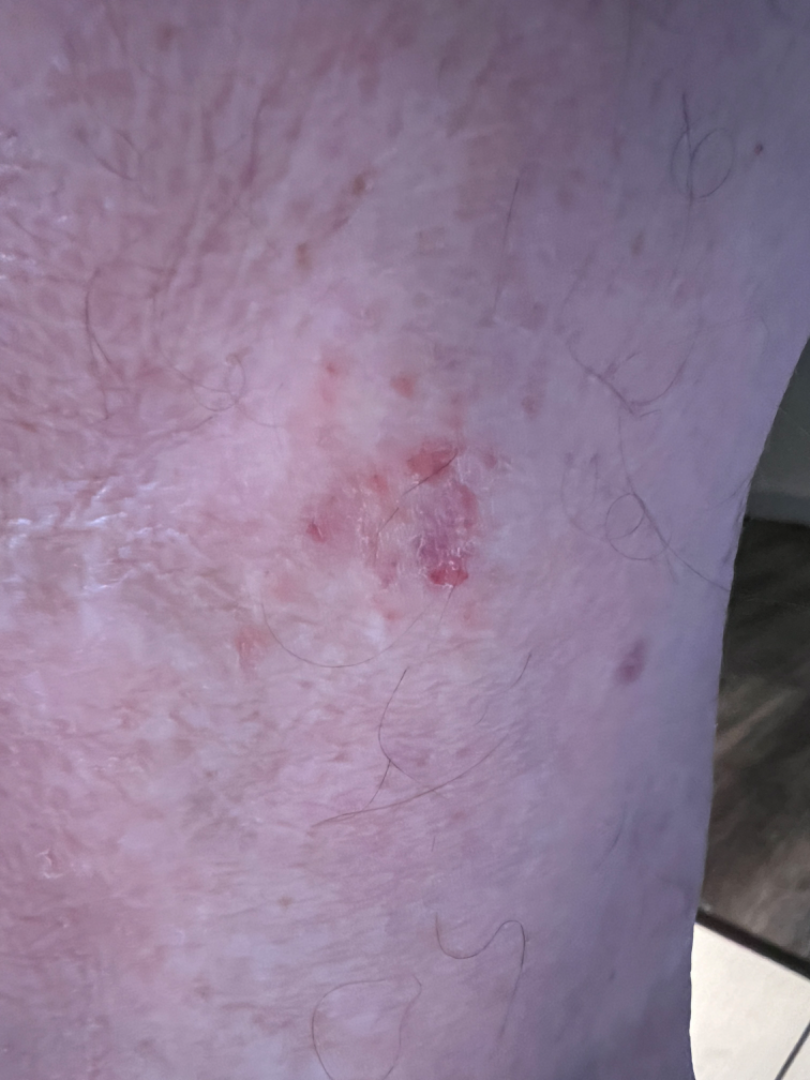{"shot_type": "close-up", "body_site": "leg", "patient": "male, age 60–69", "differential": {"leading": ["Eczema"]}}